A male patient, in their 40s; a dermoscopic close-up of a skin lesion: 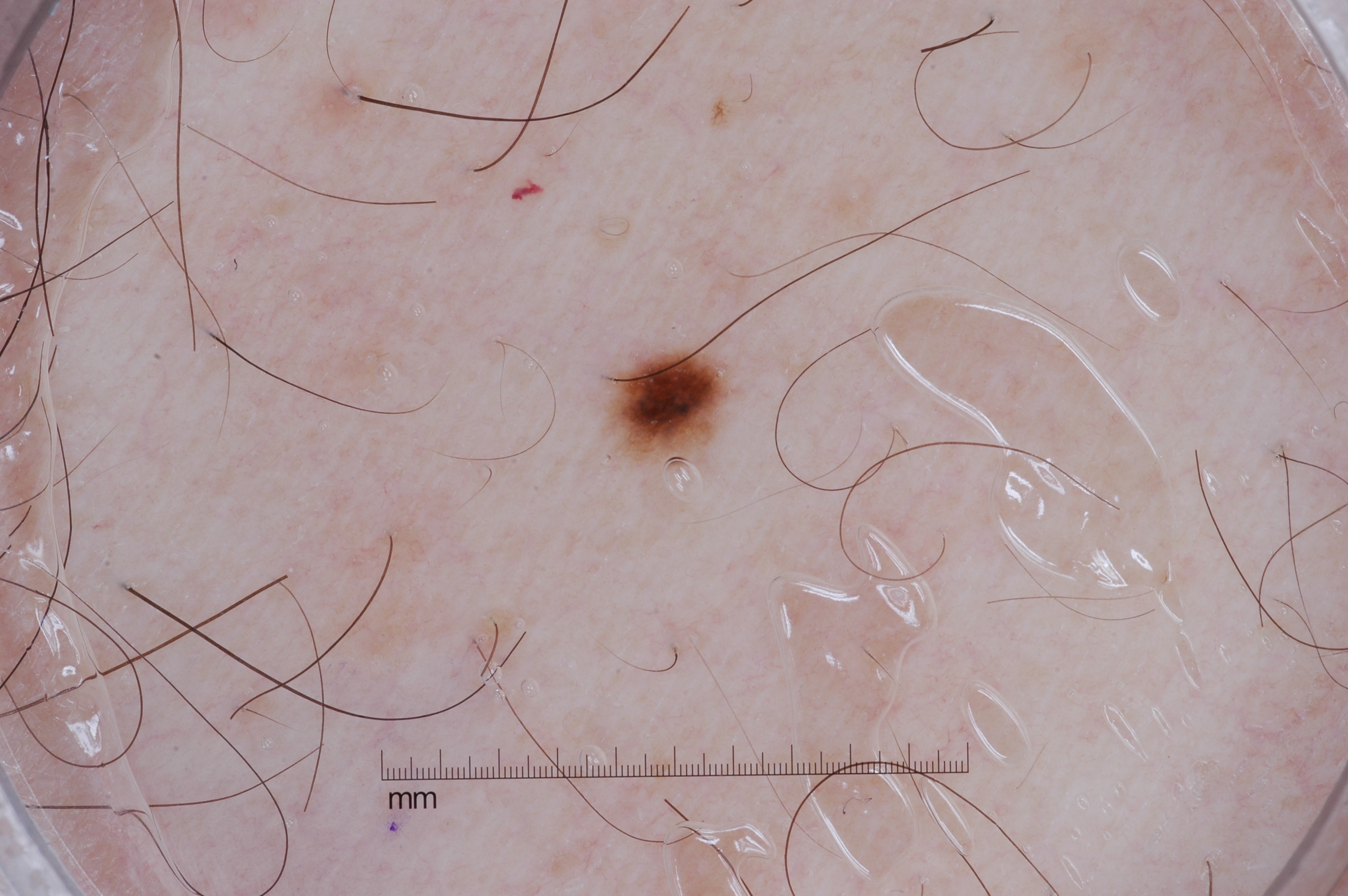Notes:
- dermoscopic features — pigment network; absent: negative network, streaks, and milia-like cysts
- bounding box — <bbox>622, 357, 716, 447</bbox>
- diagnostic label — a melanocytic nevus, a benign skin lesion